Texture is reported as raised or bumpy, no associated systemic symptoms reported, the affected area is the arm, the photograph was taken at a distance, reported duration is one to four weeks, the lesion is associated with itching.
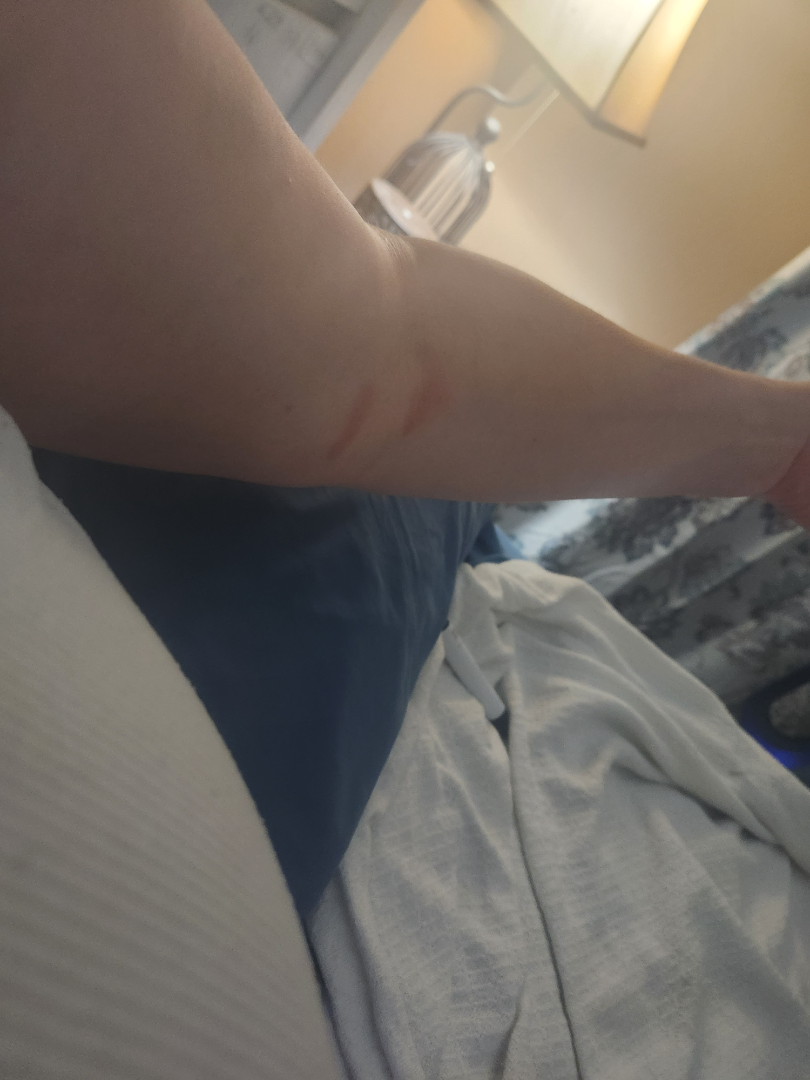The reviewing clinician's impression was: Urticaria (possible); Burn of skin (possible); Allergic Contact Dermatitis (possible).